This is a close-up image. The top or side of the foot, leg, back of the hand and arm are involved — 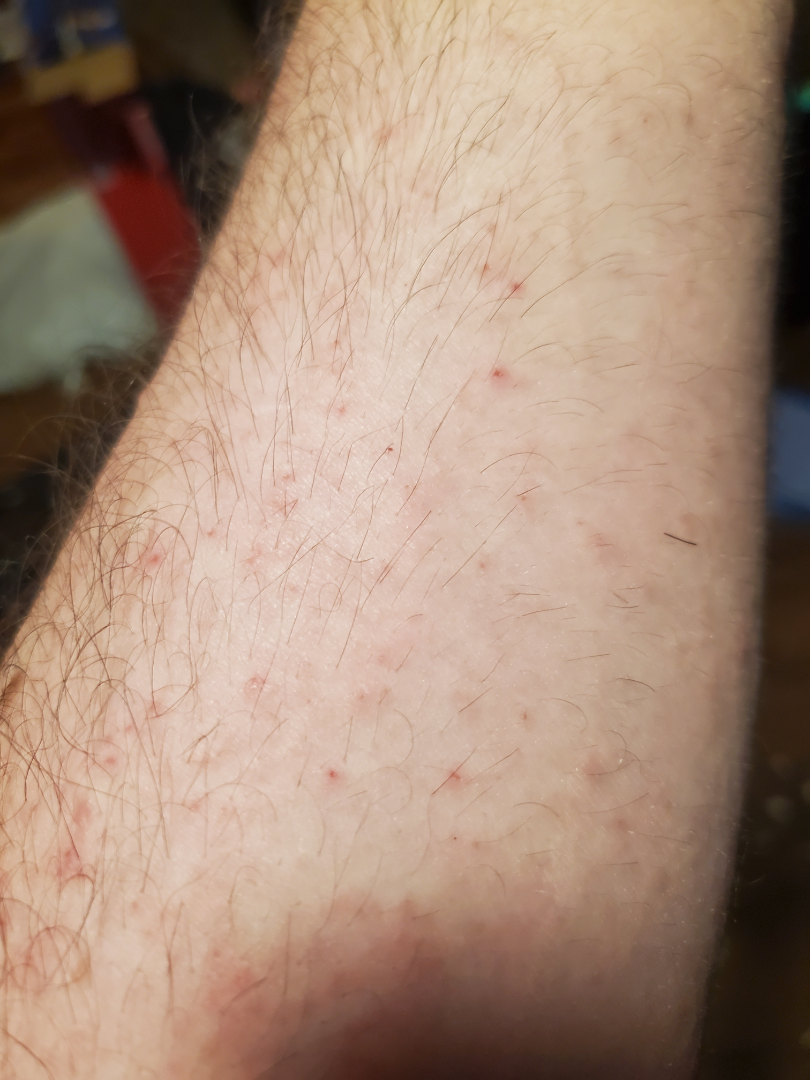lesion texture = raised or bumpy, fluid-filled and flat | symptom duration = one to four weeks | reported symptoms = enlargement, bothersome appearance, itching, burning, bleeding and pain | constitutional symptoms = none reported | patient describes the issue as = a rash | clinical impression = the differential is split between Folliculitis and Irritant Contact Dermatitis.